The patient is Fitzpatrick II. A male patient 42 years old. History notes alcohol use and no pesticide exposure: 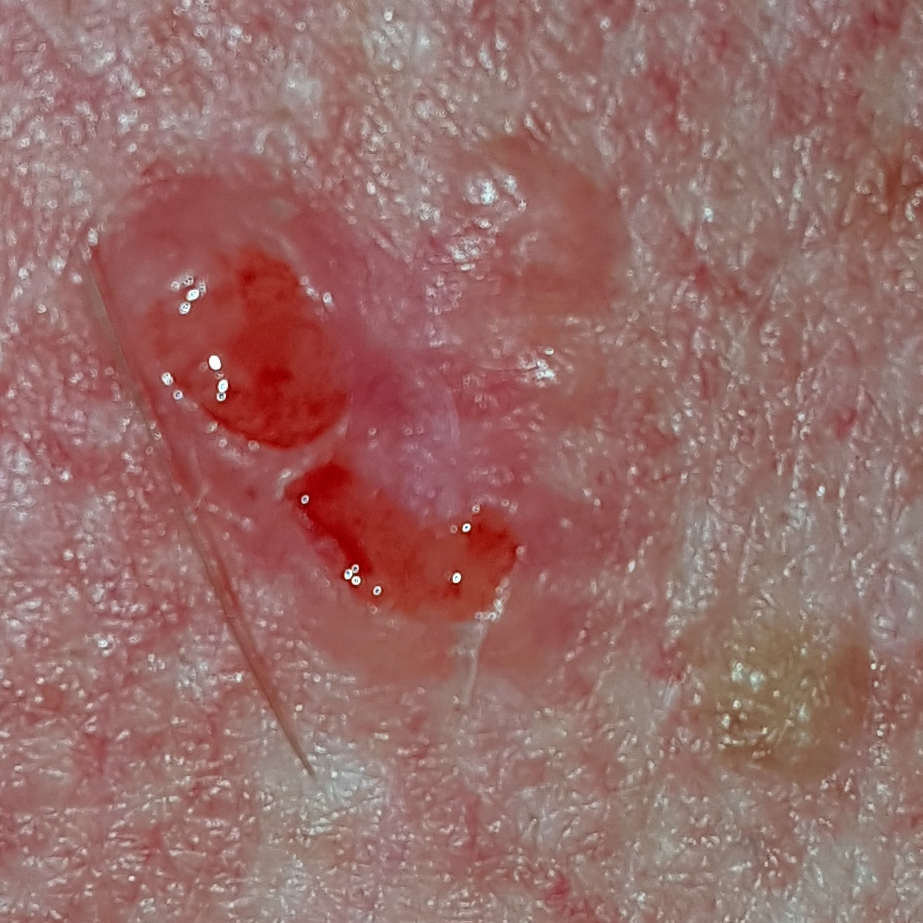The lesion is on the chest. The lesion measures approximately 12 × 6 mm. The patient describes that the lesion is elevated, has bled, itches, and hurts. On biopsy, the diagnosis was a basal cell carcinoma.